This is a close-up image · the affected area is the arm · male subject, age 30–39:
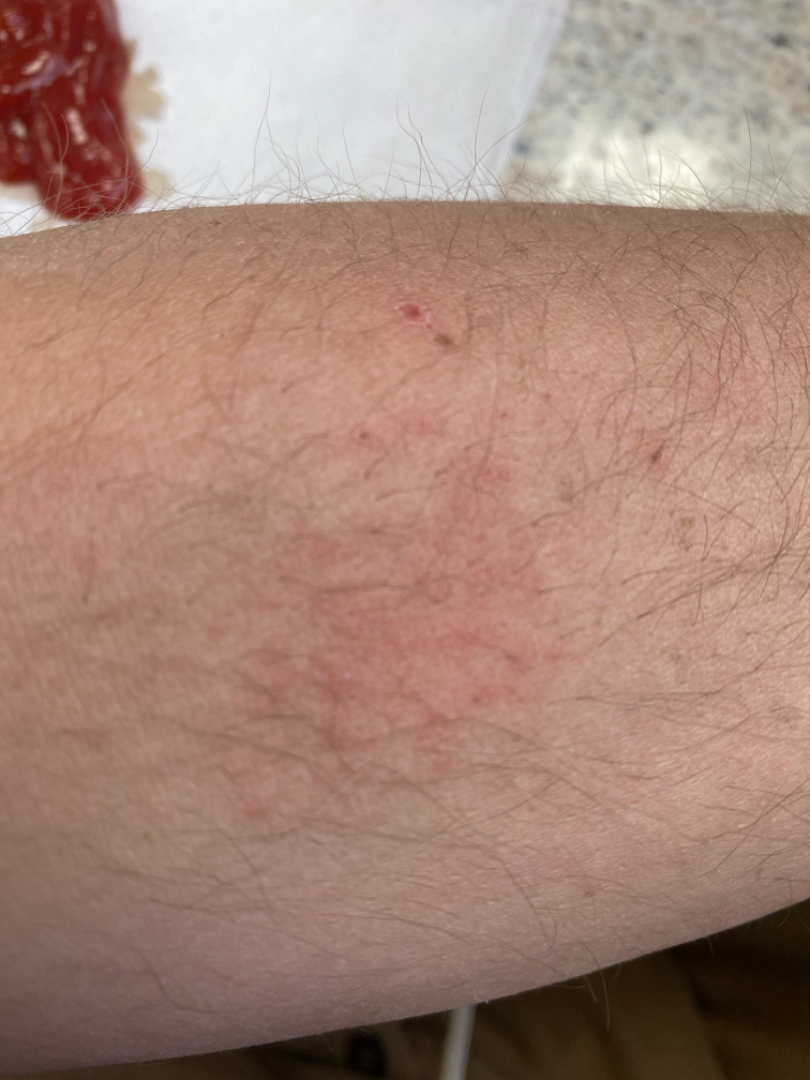Notes:
• assessment · not assessable
• skin tone · FST IV; lay reviewers estimated Monk Skin Tone 5 (US pool) or 4 (India pool)
• patient describes the issue as · a rash
• reported symptoms · itching
• duration · about one day